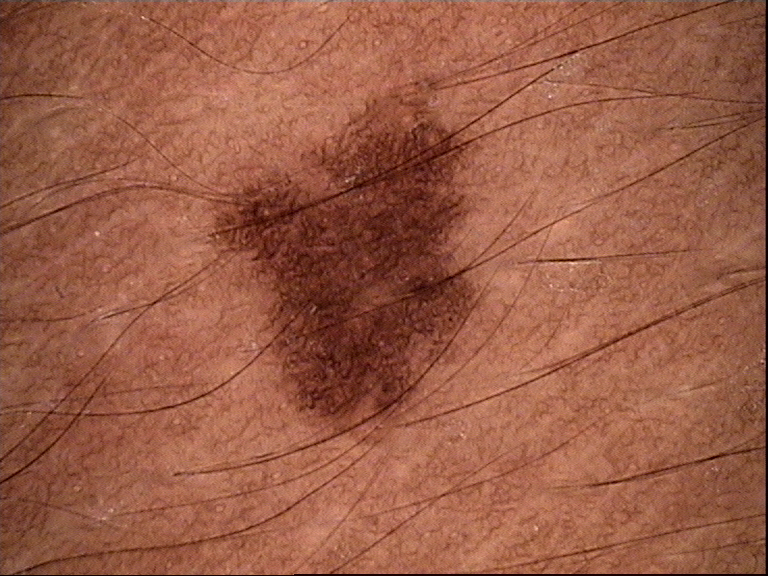Labeled as a benign lesion — a dysplastic junctional nevus.